A dermatoscopic image of a skin lesion:
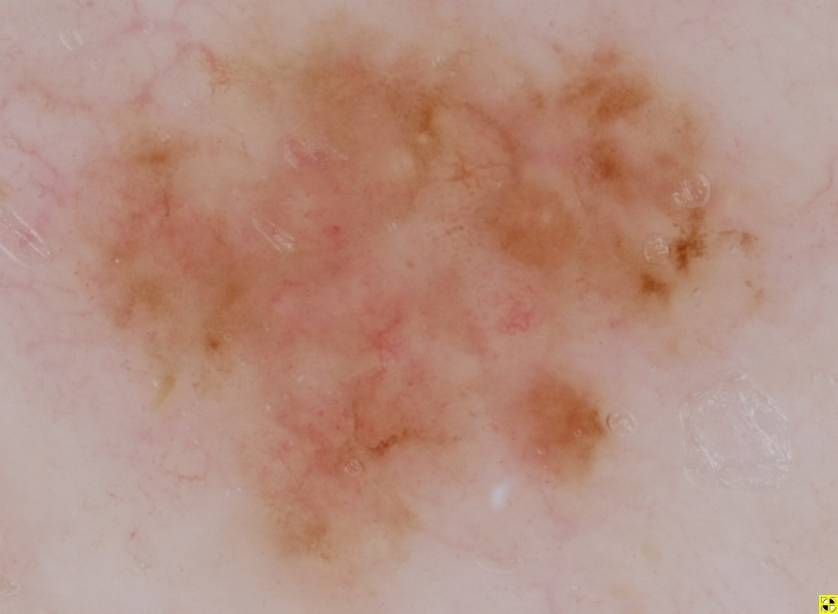Case summary:
With coordinates (x1, y1, x2, y2), the lesion's extent is <box>56, 0, 765, 587</box>. Dermoscopy demonstrates no milia-like cysts, streaks, globules, negative network, or pigment network.
Pathology:
On biopsy, the diagnosis was a melanoma.